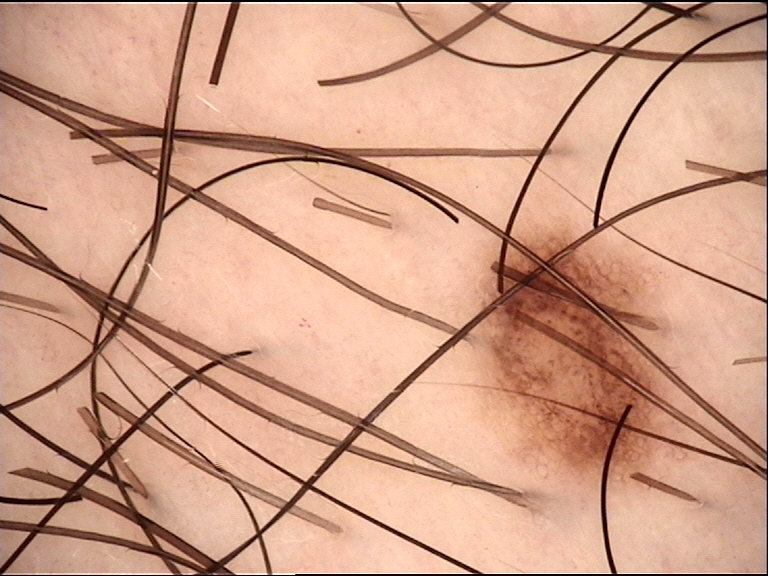Findings:
A dermatoscopic image of a skin lesion.
Impression:
Consistent with a dysplastic junctional nevus.